A clinical photograph of a skin lesion. Referred for assessment of suspected basal cell carcinoma — 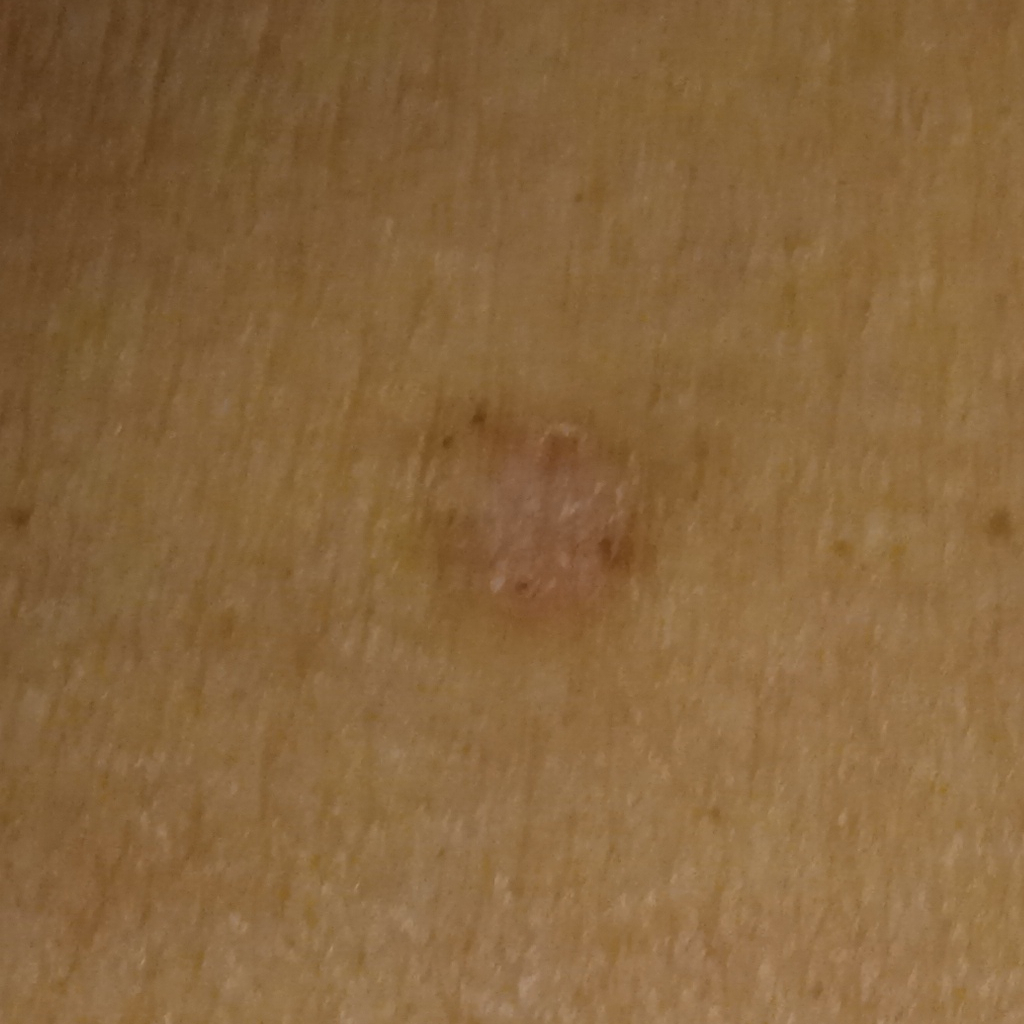| feature | finding |
|---|---|
| body site | the torso |
| size | 8.1 mm |
| diagnostic label | basal cell carcinoma (biopsy-proven) |